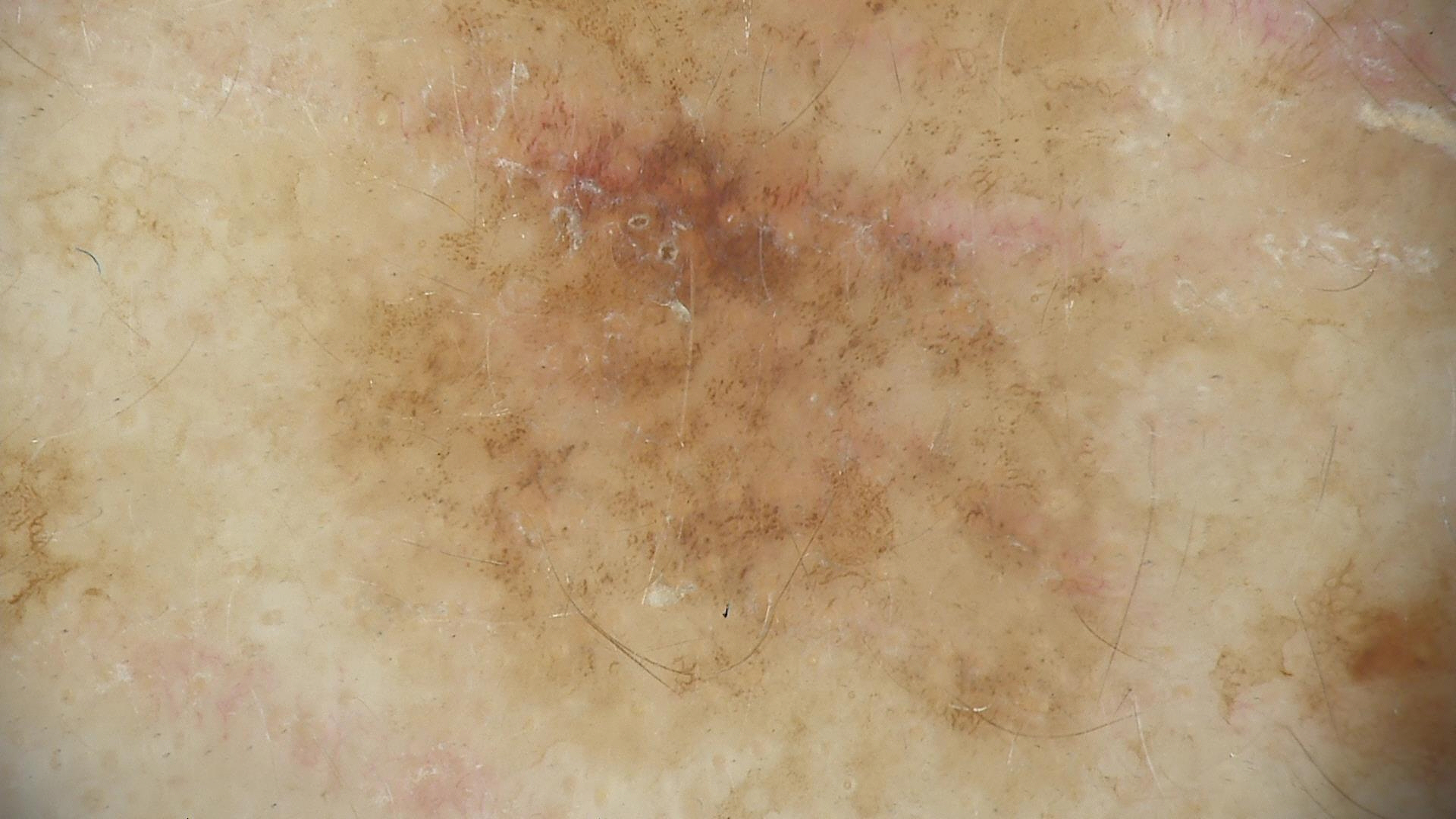diagnosis: lichenoid keratosis (expert consensus).